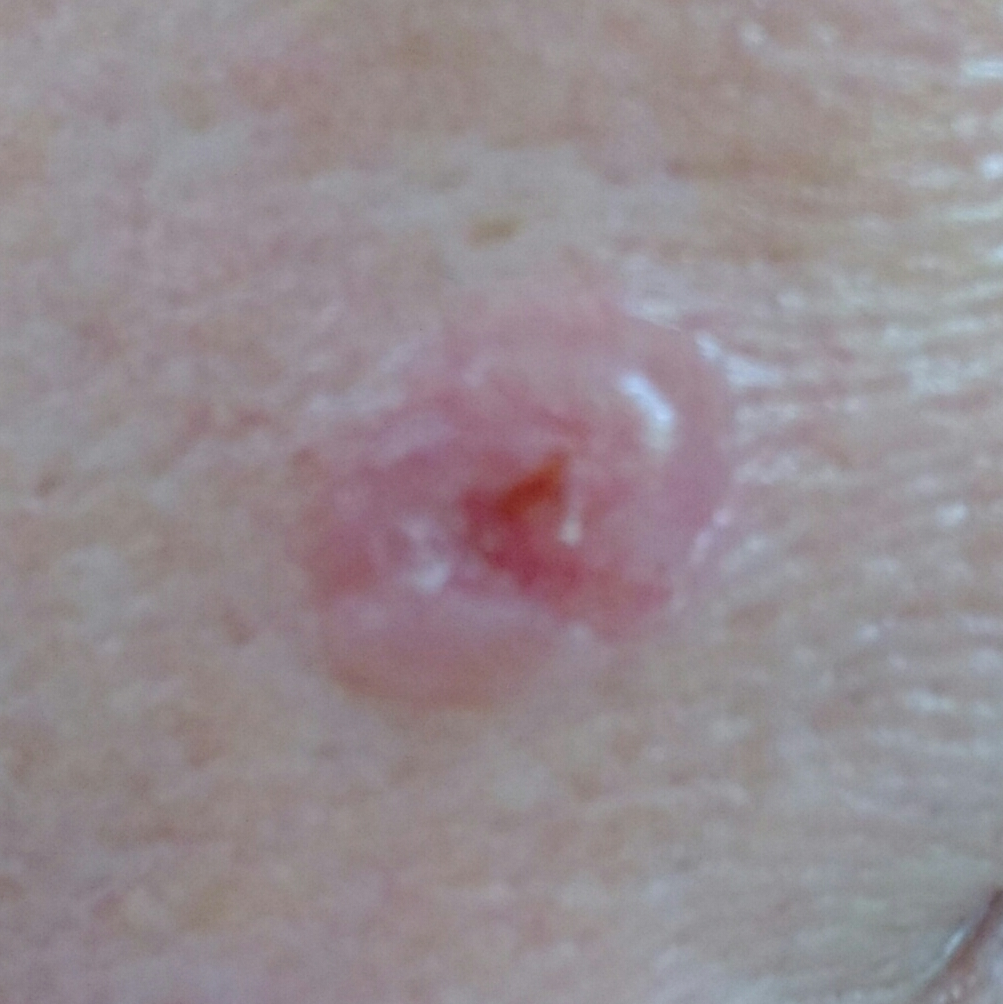The chart records prior skin cancer (patient or family) and pesticide exposure. The patient is Fitzpatrick phototype II. A clinical photograph showing a skin lesion. The lesion involves the face. The lesion measures 8 × 7 mm. The patient reports that the lesion is elevated, itches, has bled, and has grown. The biopsy diagnosis was a malignant skin lesion — a basal cell carcinoma.